The arm is involved; the subject is a female aged 18–29; the photograph is a close-up of the affected area.
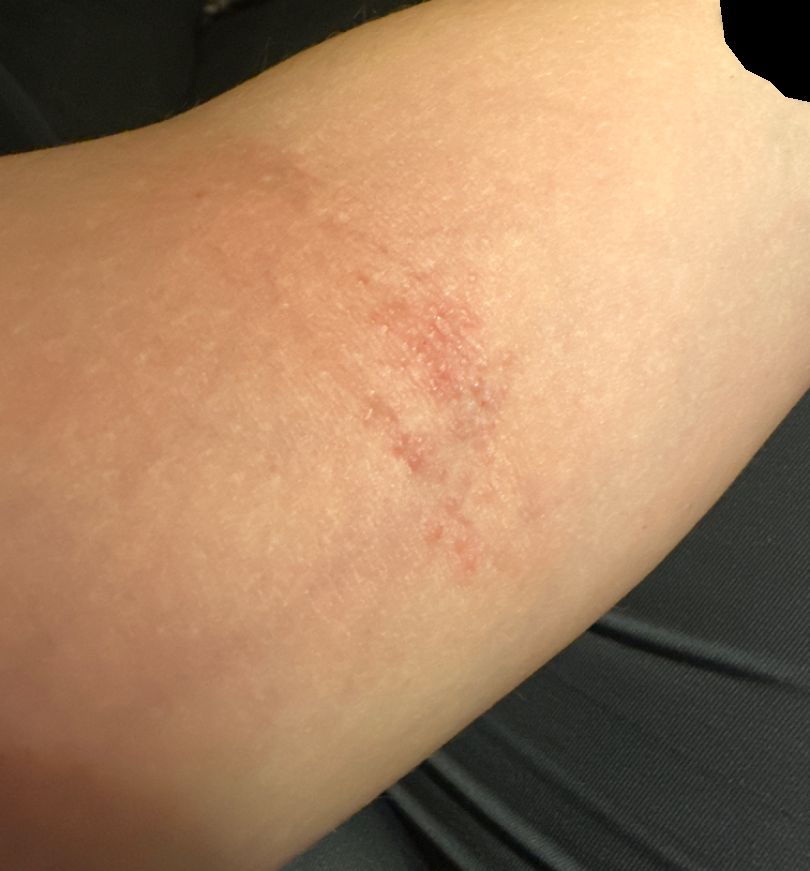{"differential": {"Eczema": 0.54, "Tinea": 0.23, "Allergic Contact Dermatitis": 0.23}}